A dermoscopic image of a skin lesion · few moles overall by the patient's own estimate · a female subject aged 71 · the referring clinician suspected basal cell carcinoma · by self-report, a personal history of skin cancer, a personal history of cancer, no sunbed use, and no family history of skin cancer.
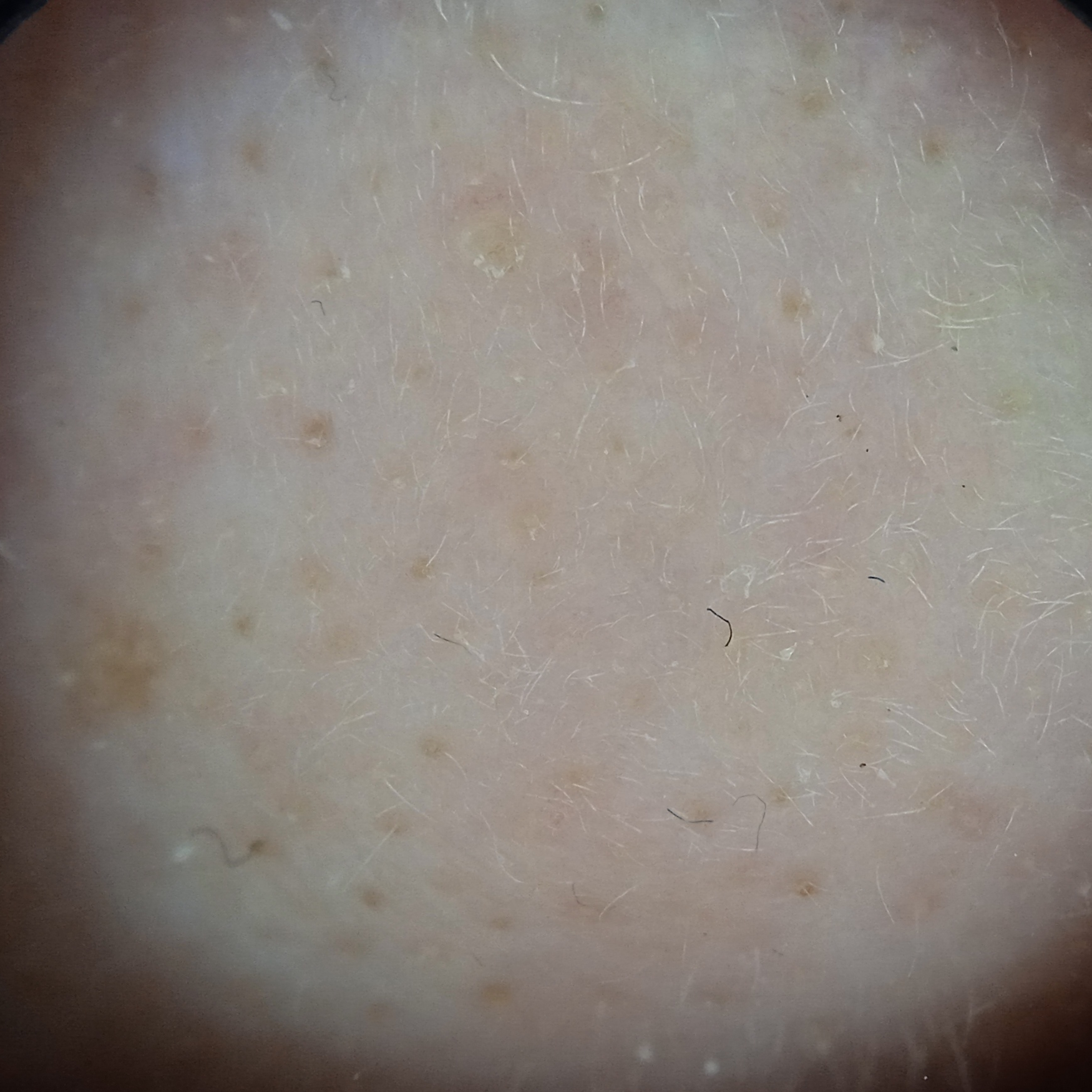Summary:
The lesion is located on the face. Measuring roughly 7.3 mm.
Conclusion:
On independent review by four dermatologists, the agreed diagnosis was an actinic keratosis; the reviewers' opinions were divided; the reviewers were moderately confident; the differential also included a seborrheic keratosis.